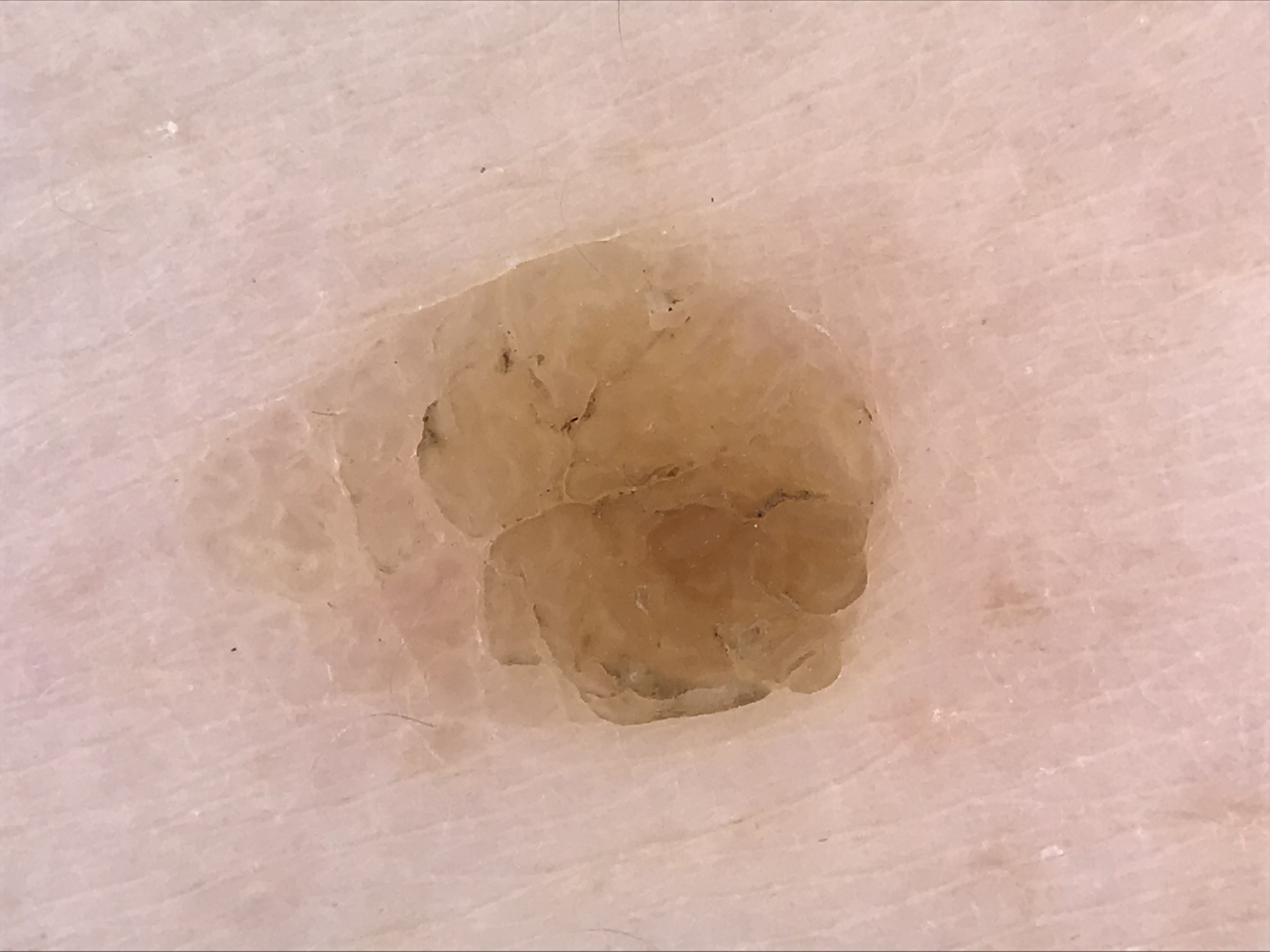– image type: dermoscopy
– category: keratinocytic
– diagnosis: seborrheic keratosis (expert consensus)